A clinical close-up photograph of a skin lesion. The patient is FST III.
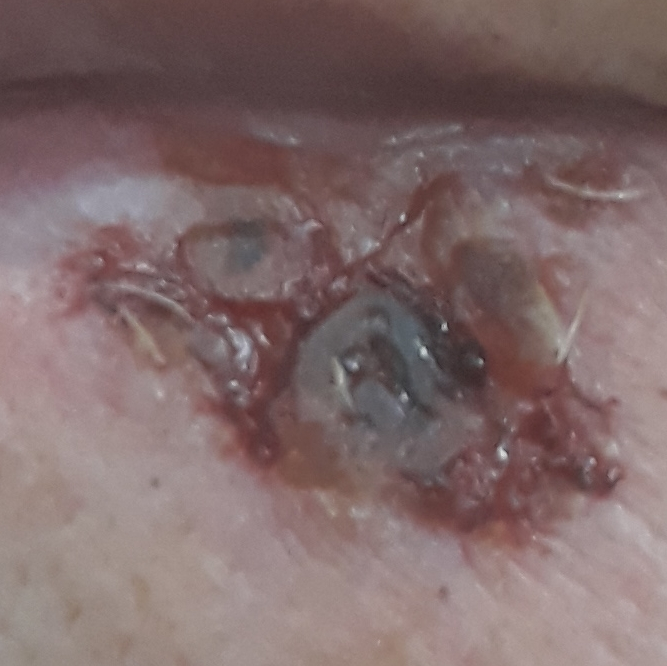The lesion is roughly 14 by 8 mm. The biopsy diagnosis was a malignant skin lesion — a basal cell carcinoma.